A dermoscopic close-up of a skin lesion.
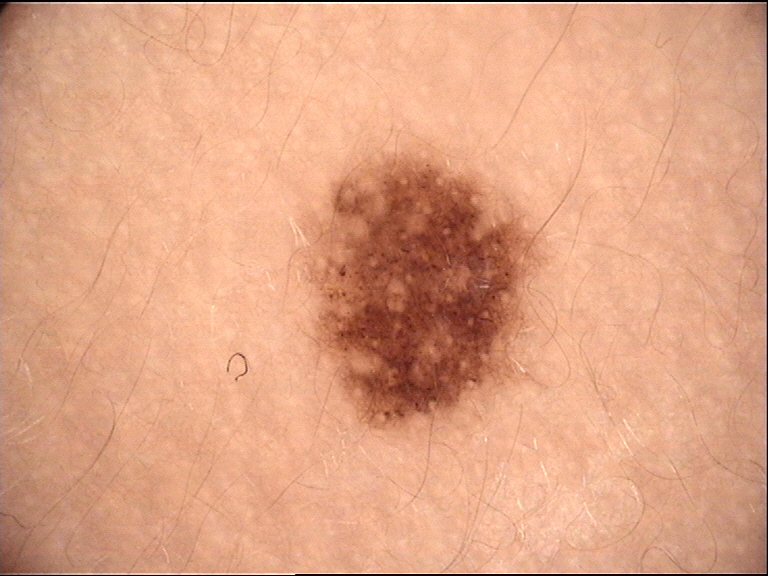diagnosis = congenital junctional nevus (expert consensus).